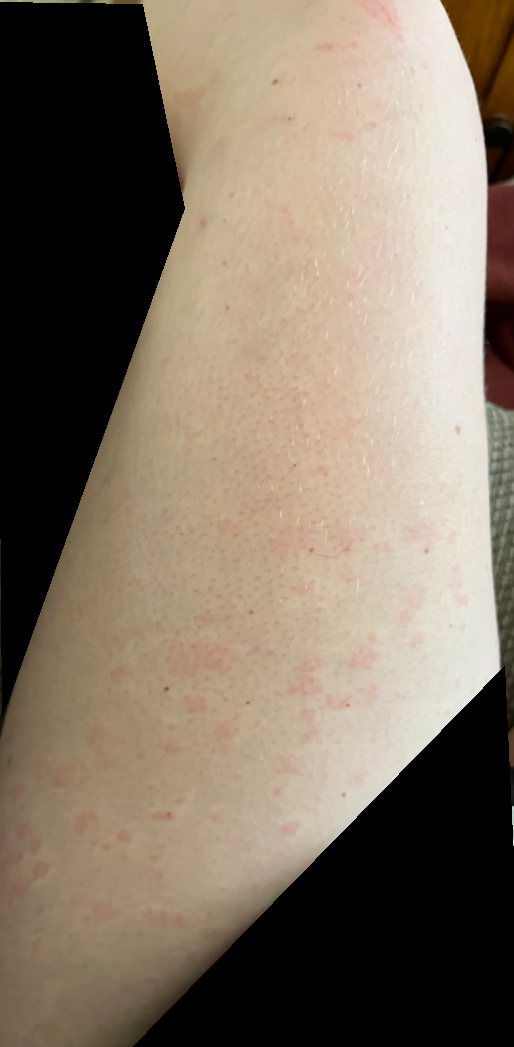Findings:
– patient · female, age 18–29
– texture · raised or bumpy
– view · at an angle
– symptoms · itching
– body site · leg and arm
– skin tone · Fitzpatrick skin type II; human graders estimated Monk Skin Tone 1 or 2
– symptom duration · less than one week
– clinical impression · the leading consideration is Urticaria; less likely is Drug Rash; lower on the differential is Viral Exanthem